A dermoscopy image of a single skin lesion: 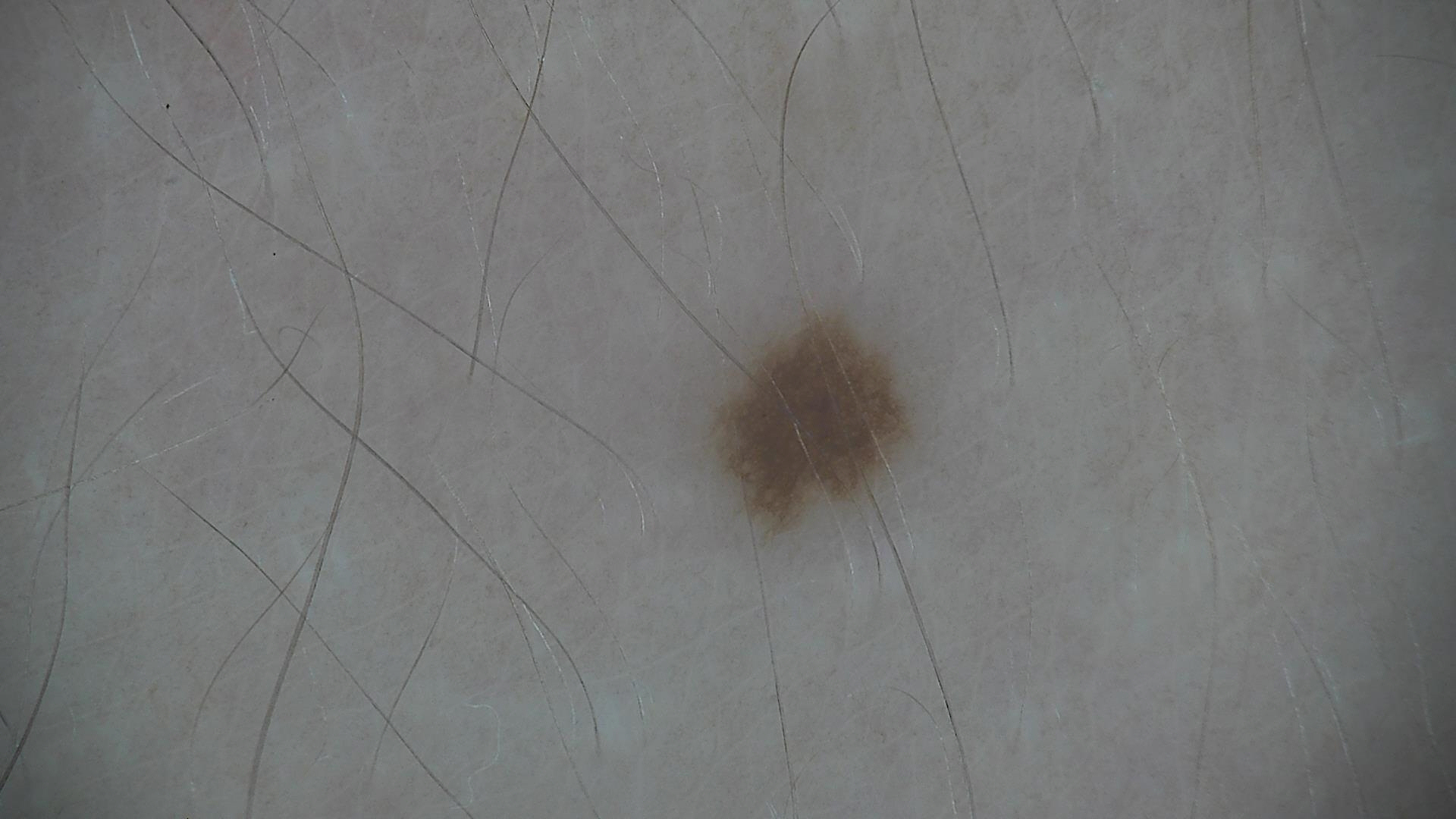The diagnosis was a benign lesion — a dysplastic junctional nevus.